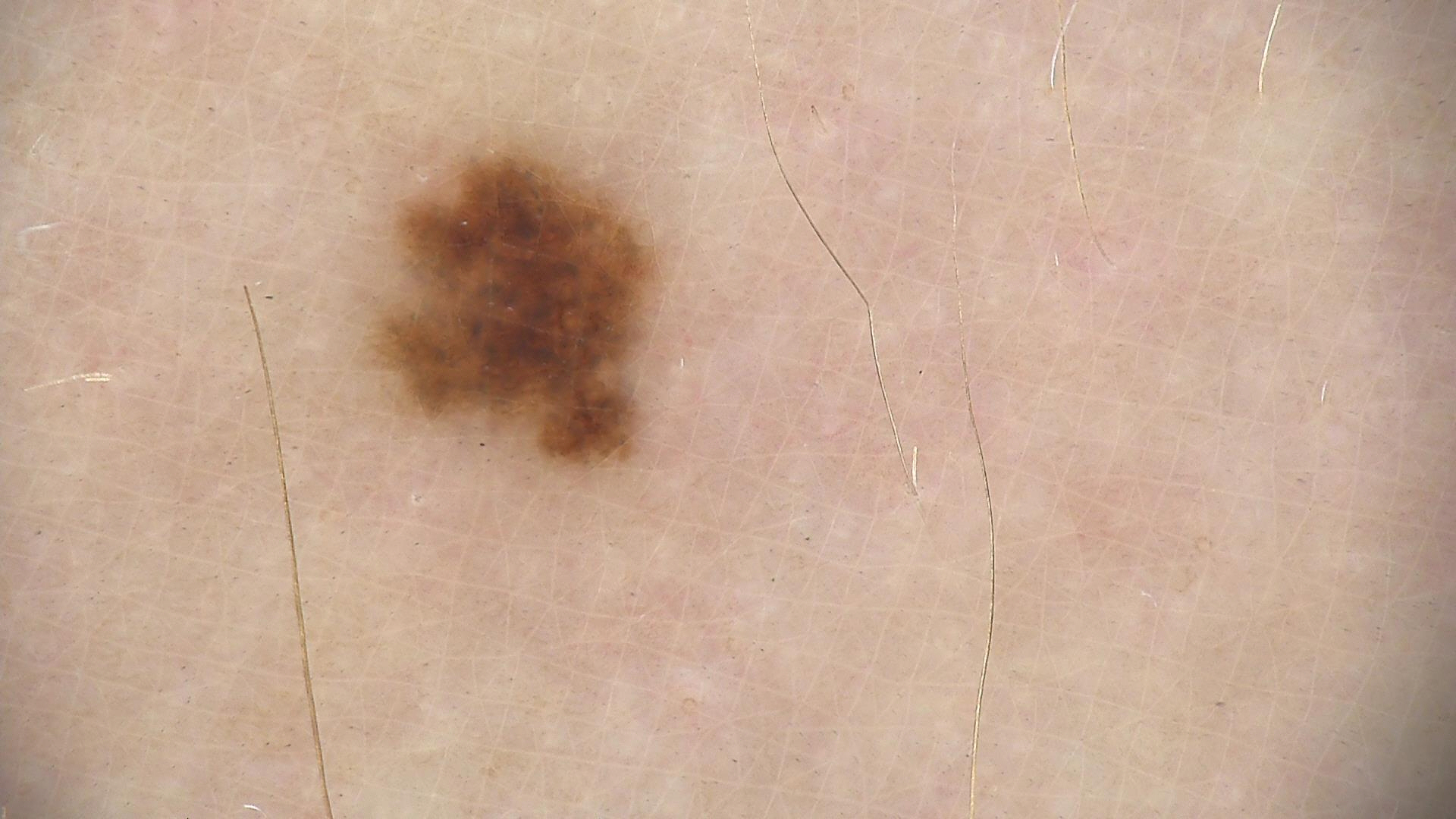image = dermoscopy; label = dysplastic junctional nevus (expert consensus).